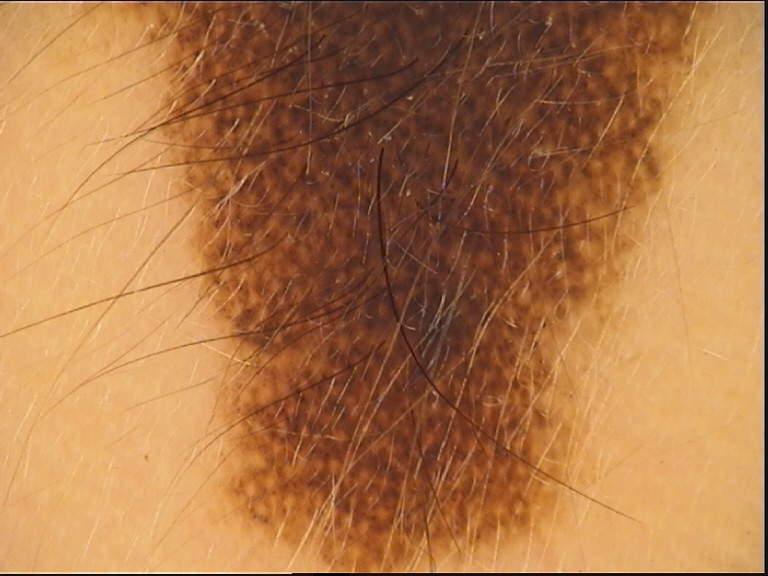<lesion>
<image>dermoscopy</image>
<diagnosis>
<name>congenital compound nevus</name>
<code>ccb</code>
<malignancy>benign</malignancy>
<super_class>melanocytic</super_class>
<confirmation>expert consensus</confirmation>
</diagnosis>
</lesion>